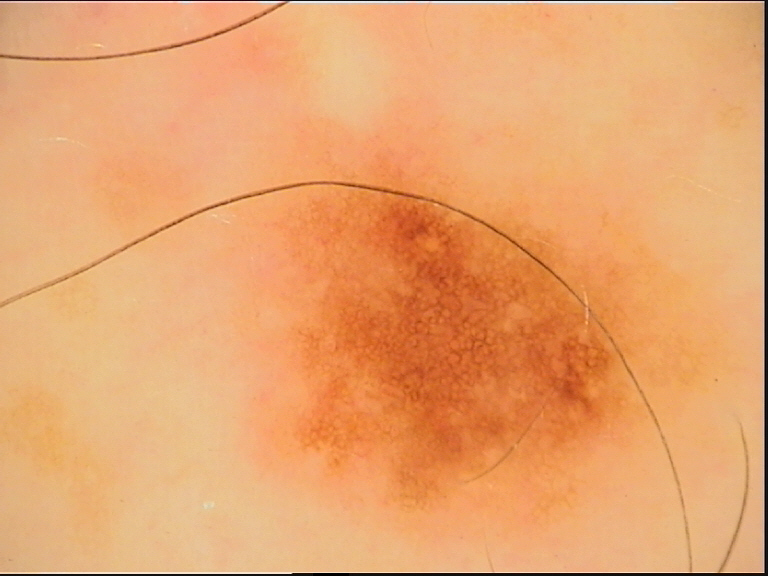The diagnosis was a dysplastic junctional nevus.